The subject is a female aged 40–49. Self-categorized by the patient as a rash. The lesion is associated with itching. A close-up photograph. Skin tone: Fitzpatrick II; non-clinician graders estimated Monk Skin Tone 2. Reported duration is less than one week. Located on the head or neck:
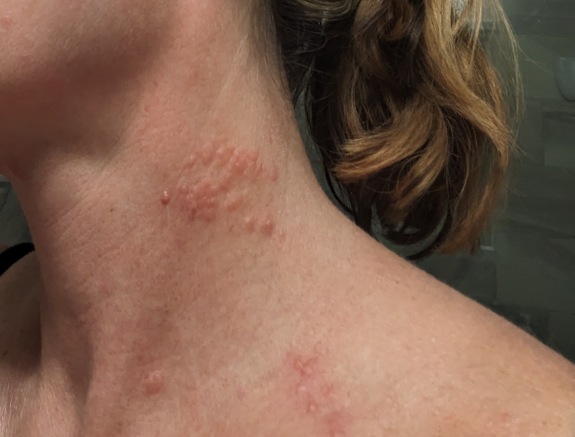differential — Herpes Zoster (primary); Contact dermatitis (possible).